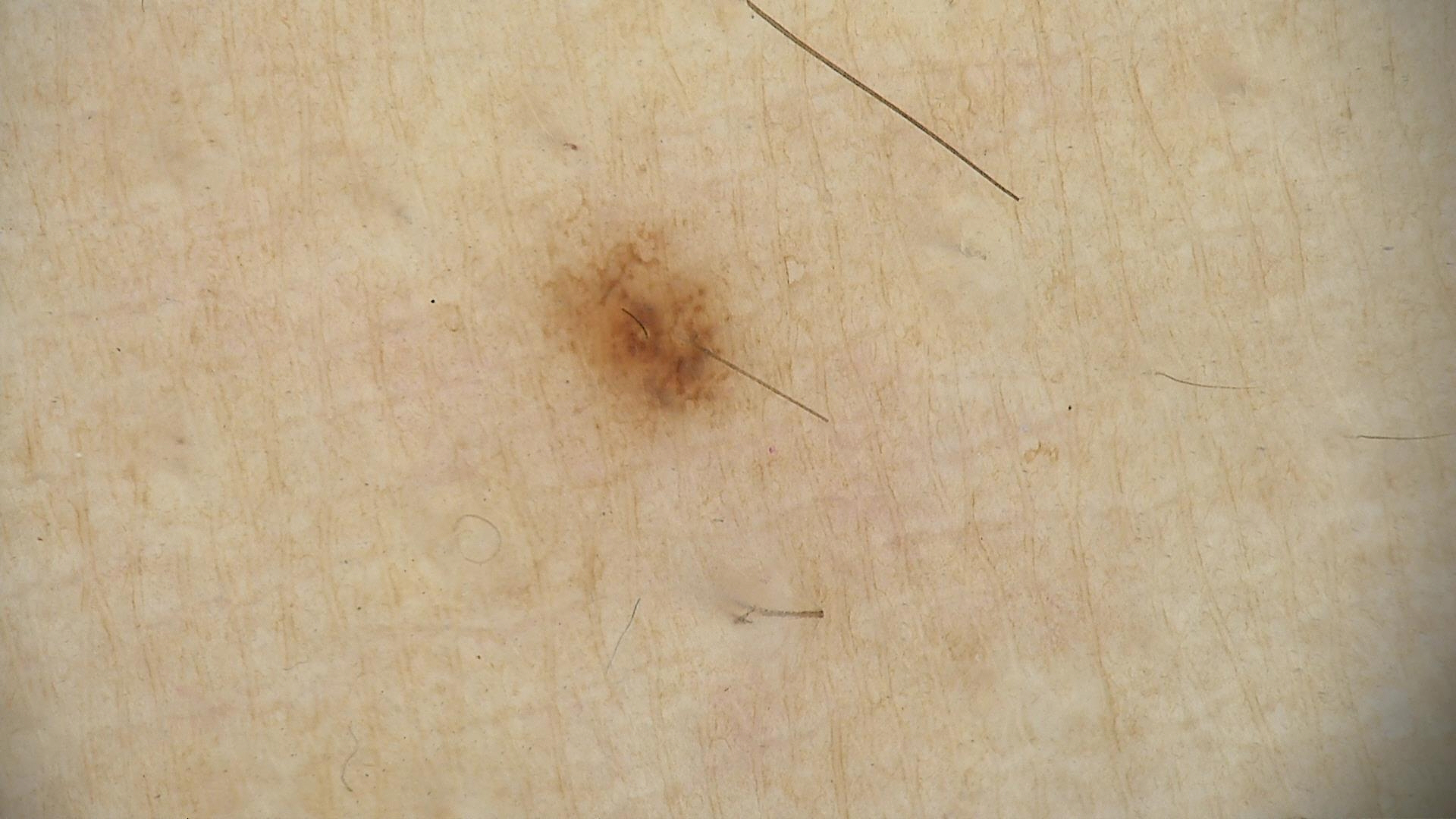The diagnosis was a dysplastic junctional nevus.